A dermoscopy image of a single skin lesion: 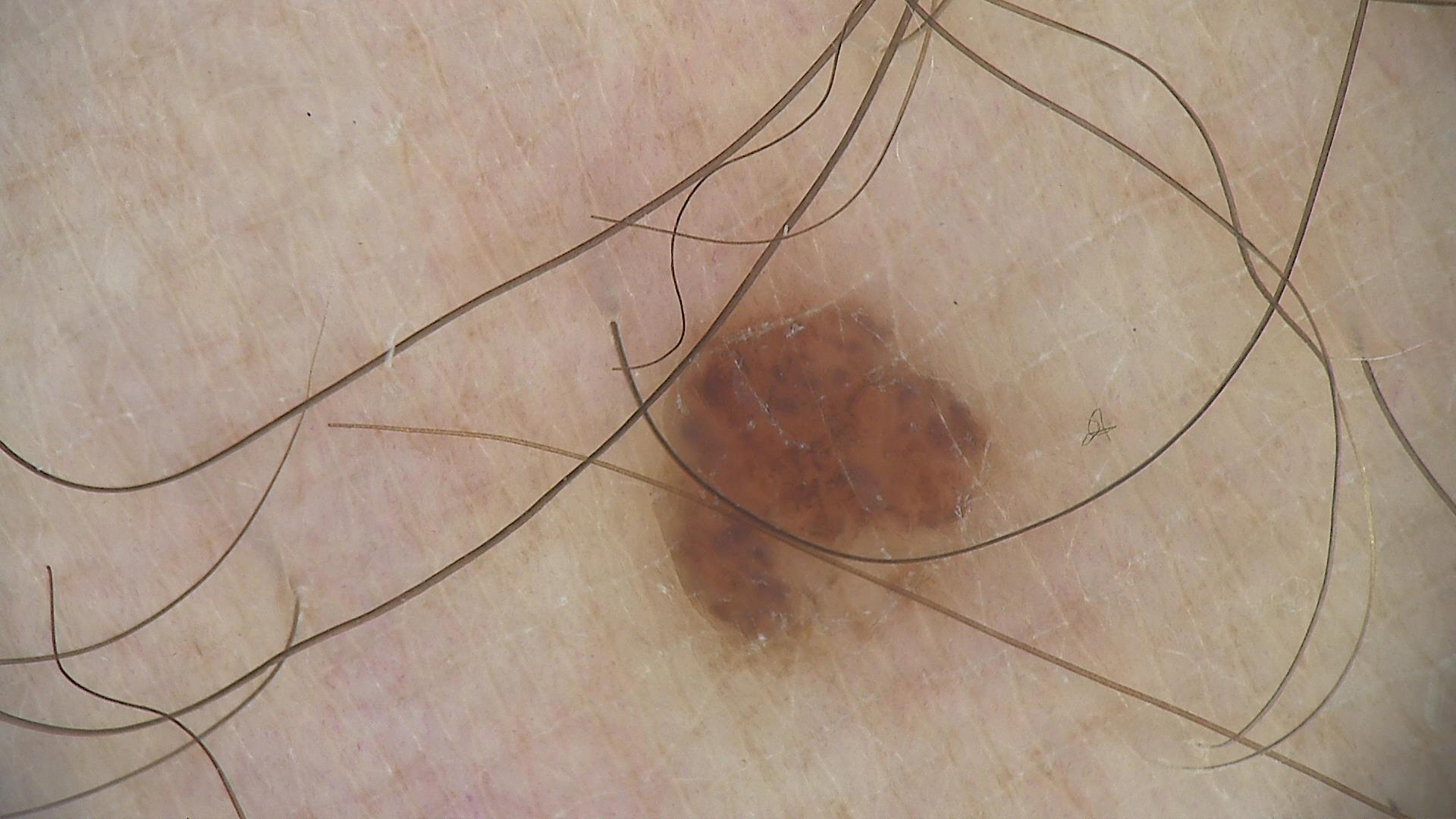{"diagnosis": {"name": "dysplastic compound nevus", "code": "cd", "malignancy": "benign", "super_class": "melanocytic", "confirmation": "expert consensus"}}